The affected area is the arm; the photograph is a close-up of the affected area; the contributor is a female aged 18–29.
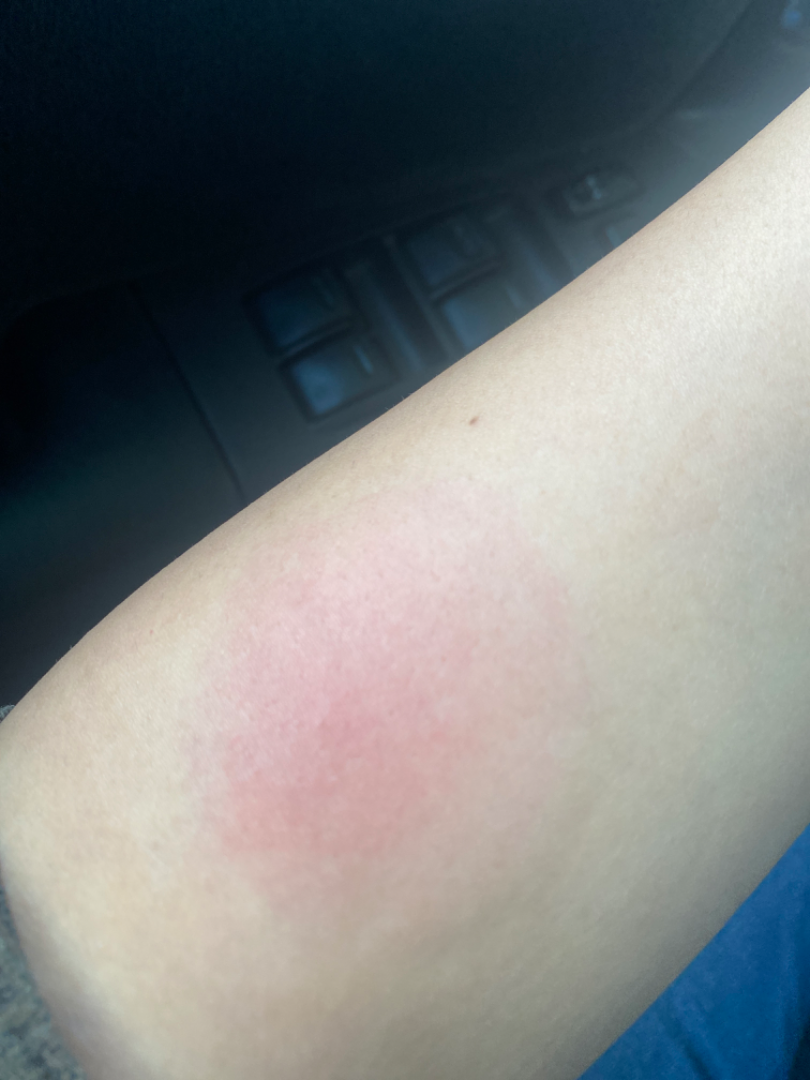The patient described the issue as skin that appeared healthy to them.
The lesion is described as raised or bumpy.
Present for less than one week.
No constitutional symptoms were reported.
On remote review of the image, the leading impression is Insect Bite; also consider Erythema annulare centrifugum.